A dermoscopic close-up of a skin lesion.
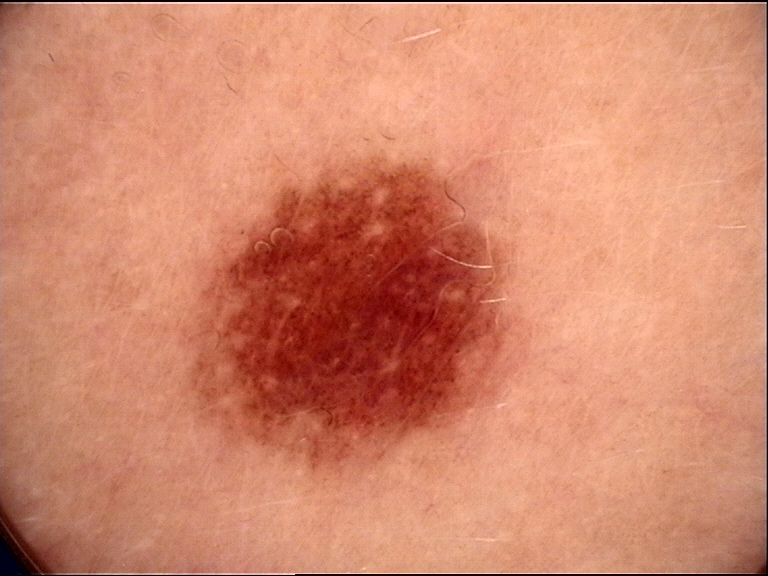Diagnosed as a dysplastic junctional nevus.